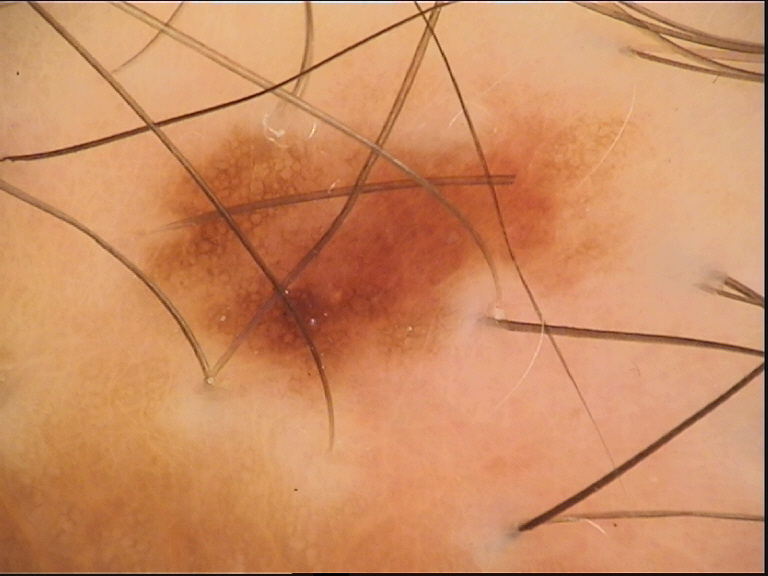Q: What is the imaging modality?
A: dermoscopy
Q: What is the diagnosis?
A: dysplastic junctional nevus (expert consensus)